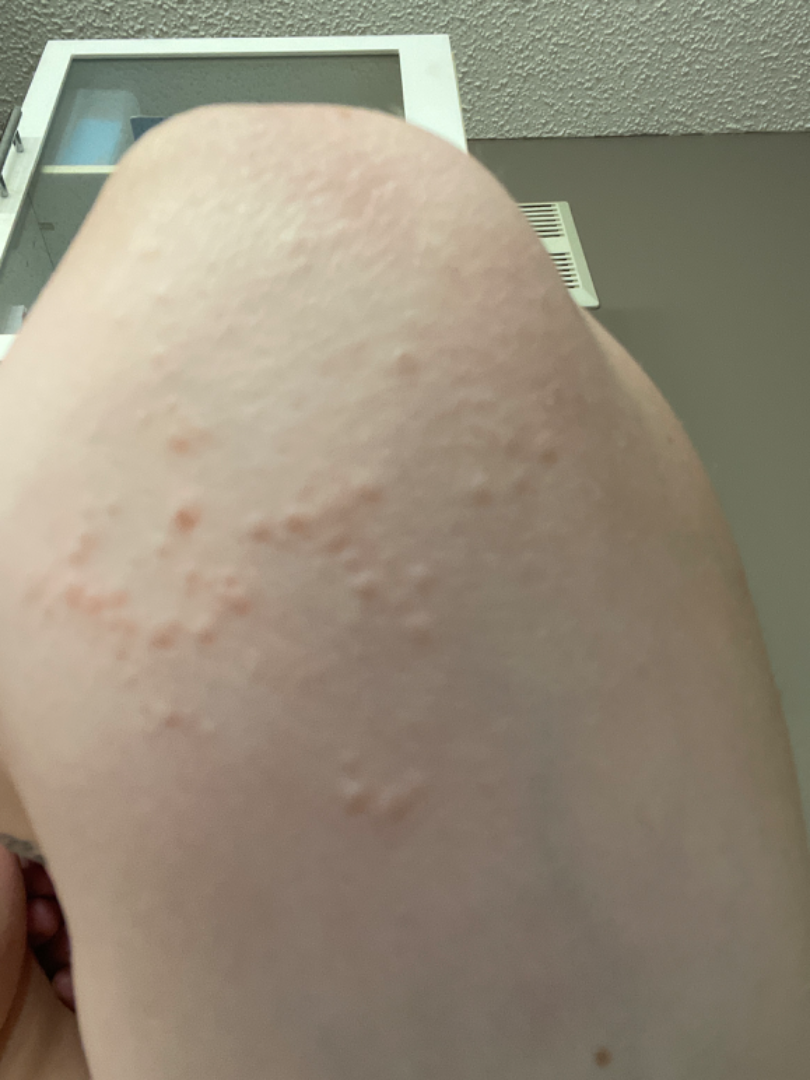Review: The case was indeterminate on photographic review. Patient information: The arm is involved. A close-up photograph.